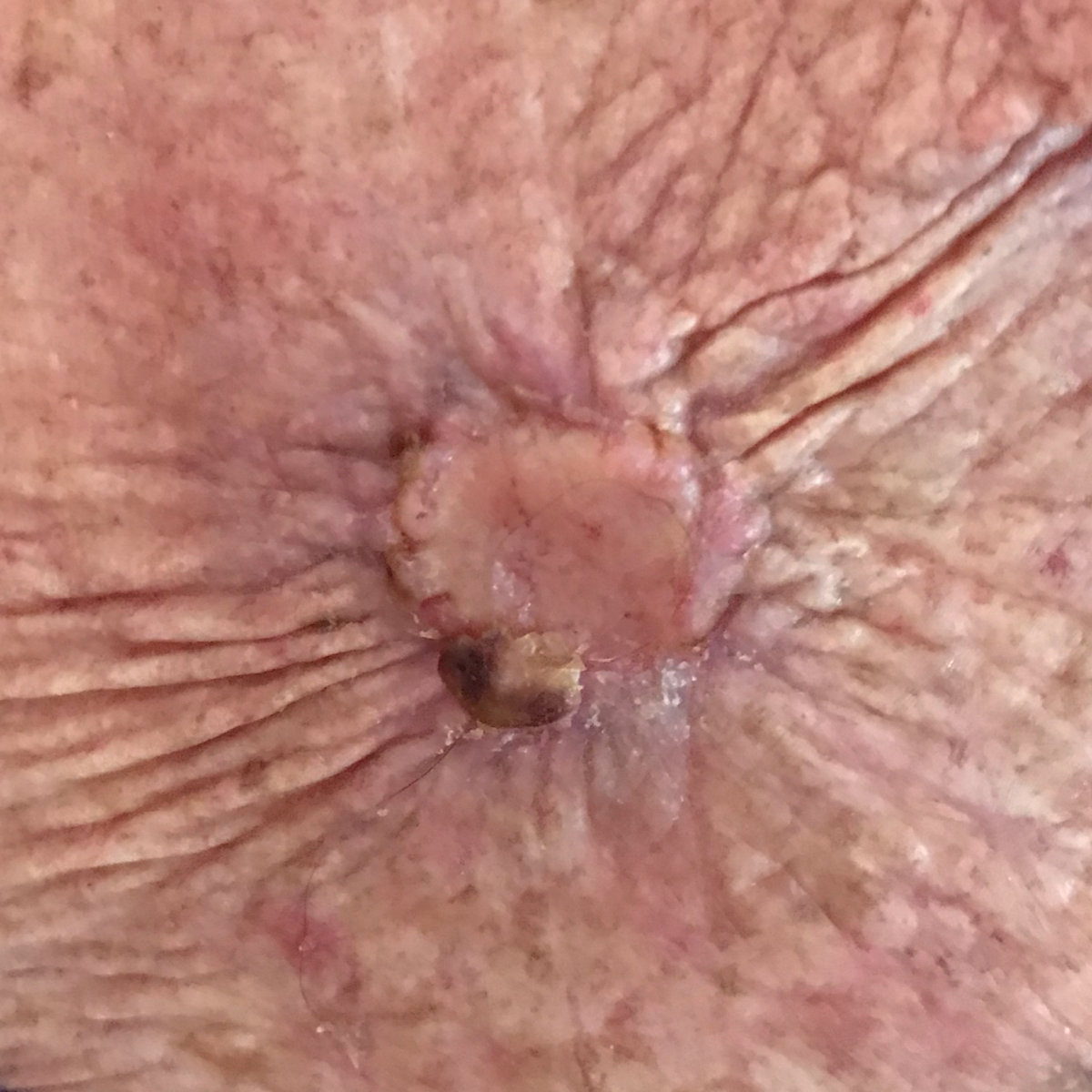<skin_lesion>
  <risk_factors>
    <positive>prior cancer (patient or family), prior skin cancer (patient or family)</positive>
  </risk_factors>
  <image>clinical photo</image>
  <skin_type>II</skin_type>
  <patient>
    <age>78</age>
    <gender>female</gender>
  </patient>
  <lesion_location>the chest</lesion_location>
  <lesion_size>
    <diameter_1_mm>20.0</diameter_1_mm>
    <diameter_2_mm>18.0</diameter_2_mm>
  </lesion_size>
  <symptoms>
    <present>change in appearance, pain, itching, growth, bleeding, elevation</present>
  </symptoms>
  <diagnosis>
    <name>basal cell carcinoma</name>
    <code>BCC</code>
    <malignancy>malignant</malignancy>
    <confirmation>histopathology</confirmation>
  </diagnosis>
</skin_lesion>